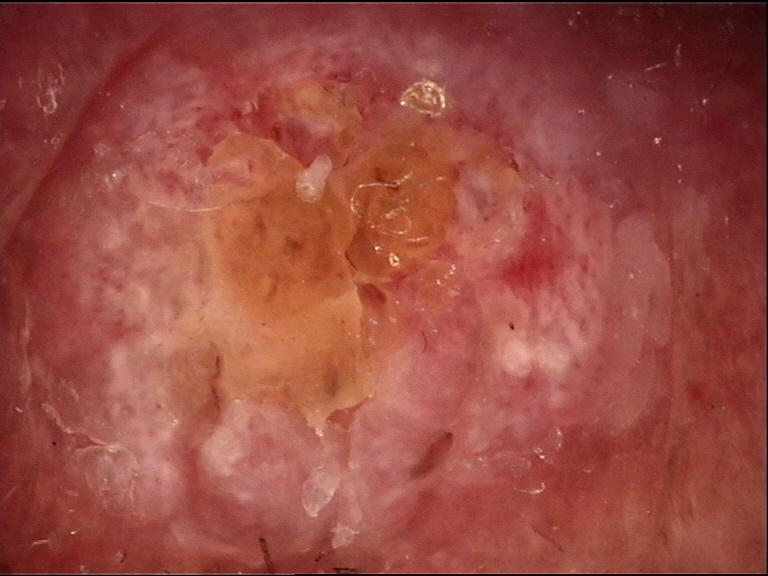class=squamous cell carcinoma (biopsy-proven).